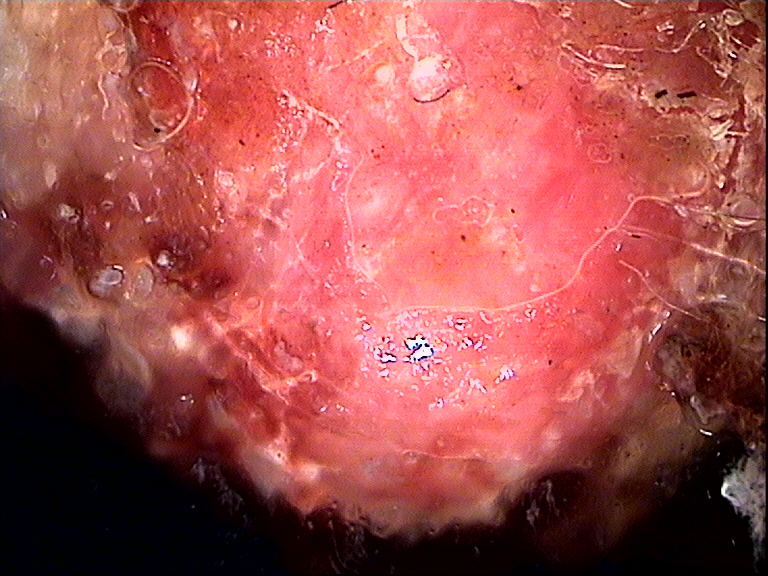Q: What is this lesion?
A: melanoma (biopsy-proven)